A dermoscopic photograph of a skin lesion:
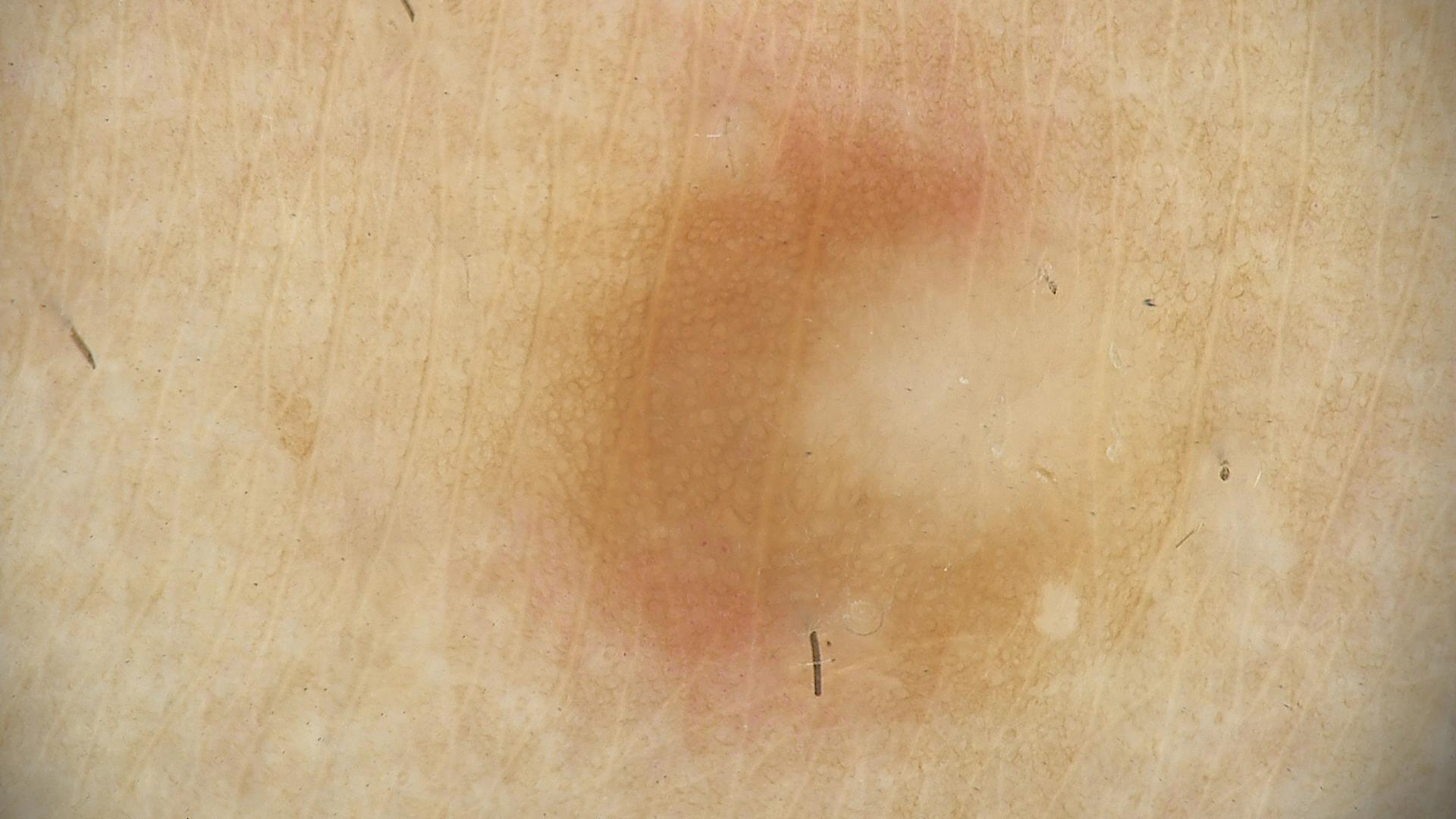{"lesion_type": {"main_class": "fibro-histiocytic"}, "diagnosis": {"name": "dermatofibroma", "code": "df", "malignancy": "benign", "super_class": "non-melanocytic", "confirmation": "expert consensus"}}